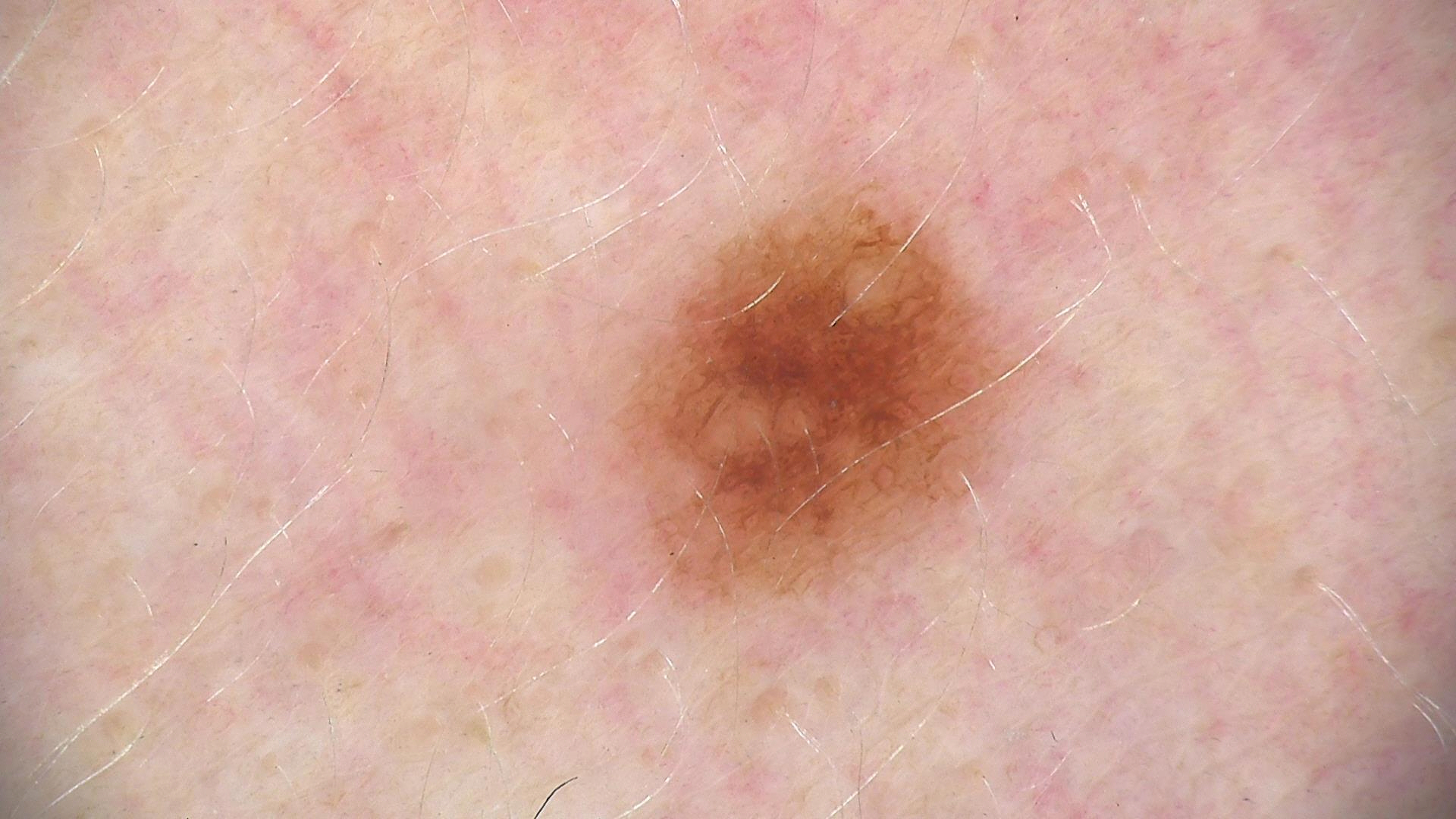Impression:
The diagnosis was a dysplastic compound nevus.